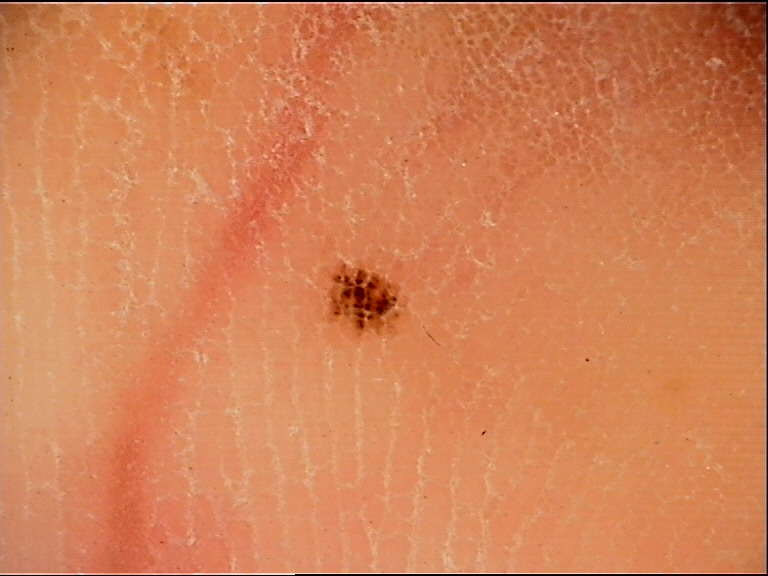Dermoscopy of a skin lesion.
Diagnosed as an acral dysplastic junctional nevus.